A clinical photograph showing a skin lesion; a male subject in their mid-80s; skin type II; history notes prior malignancy (patient or family), prior skin cancer (patient or family), alcohol use, no pesticide exposure, and no tobacco use — 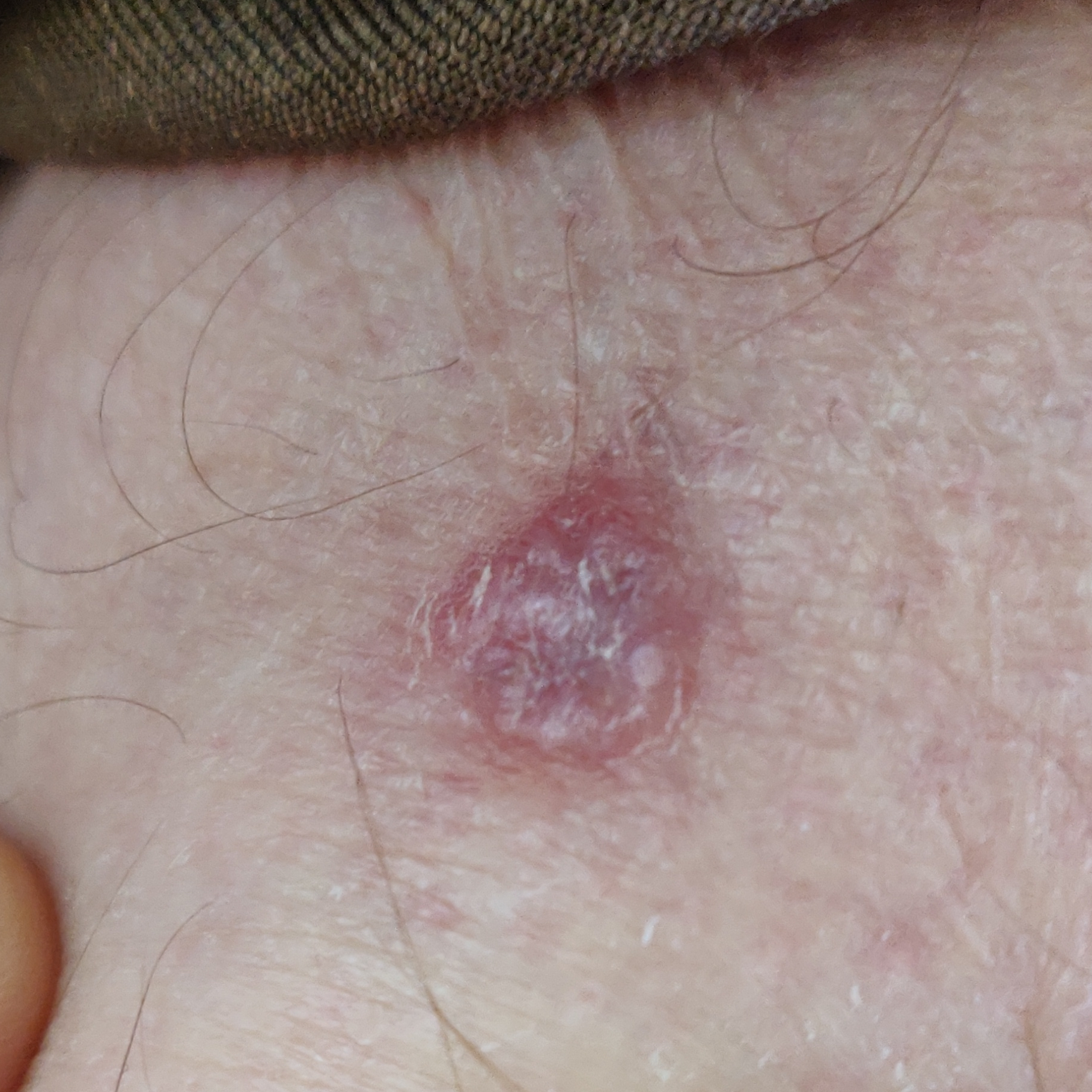Clinical context:
The lesion was found on a thigh. The lesion measures 11 × 10 mm. The patient reports that the lesion has changed, is elevated, and has grown.
Conclusion:
Histopathology confirmed a basal cell carcinoma.